The patient is a female approximately 35 years of age, a dermatoscopic image of a skin lesion.
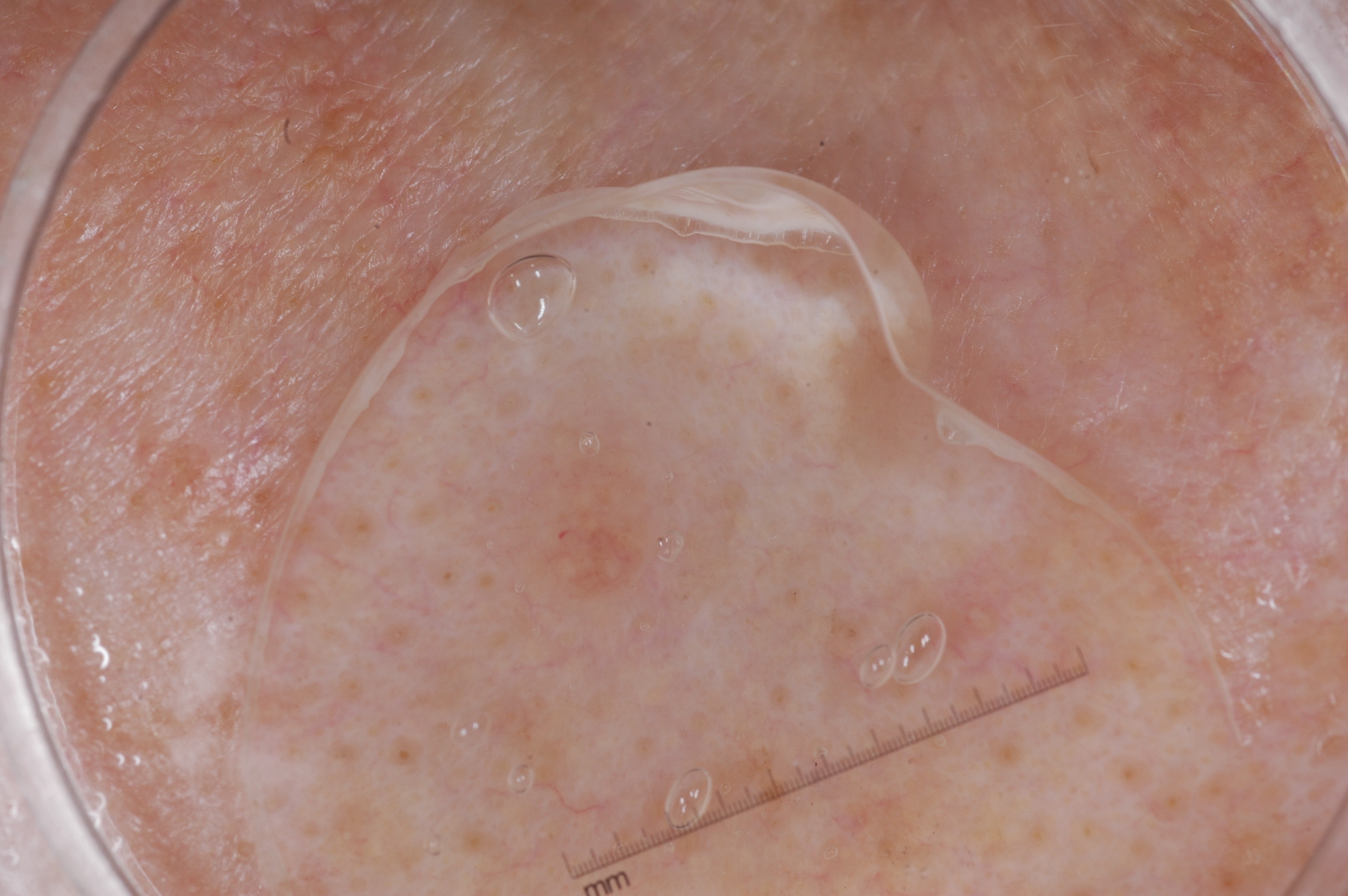The lesion occupies the region 485, 392, 884, 650. Dermoscopic examination shows no streaks, negative network, milia-like cysts, or pigment network. The lesion was assessed as a melanocytic nevus, a benign skin lesion.